A dermoscopic close-up of a skin lesion.
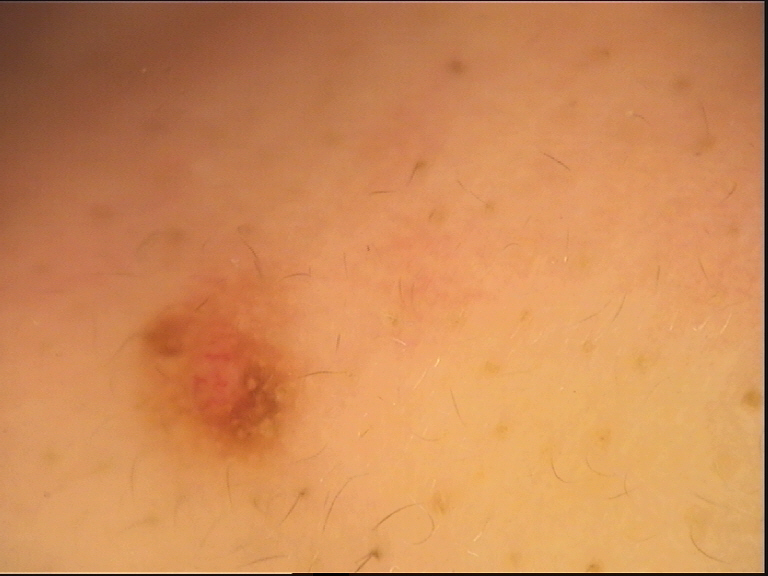Case:
* category: banal
* class: compound nevus (expert consensus)